A close-up photograph.
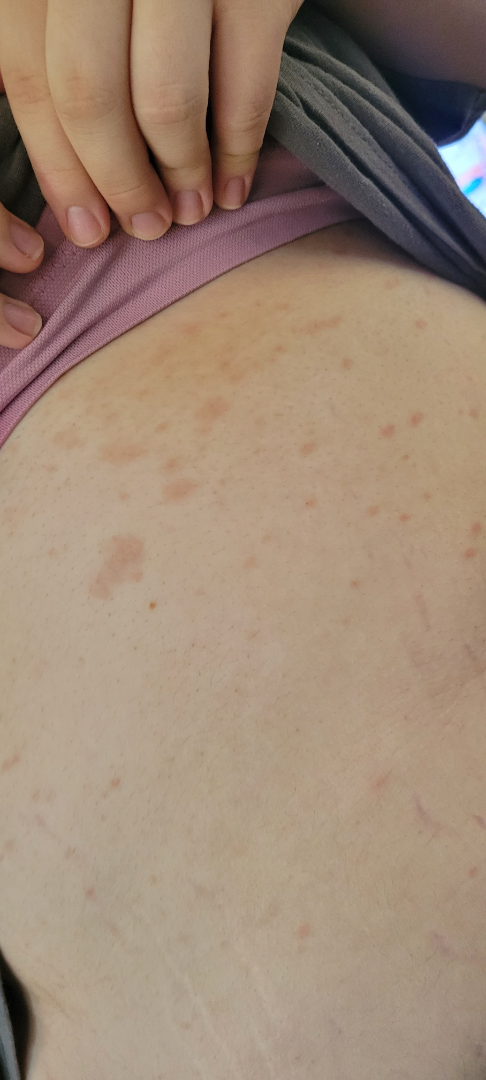Q: Fitzpatrick or Monk tone?
A: Fitzpatrick phototype II
Q: What is the dermatologist's impression?
A: Pityriasis rosea, Tinea Versicolor and Psoriasis were each considered, in no particular order